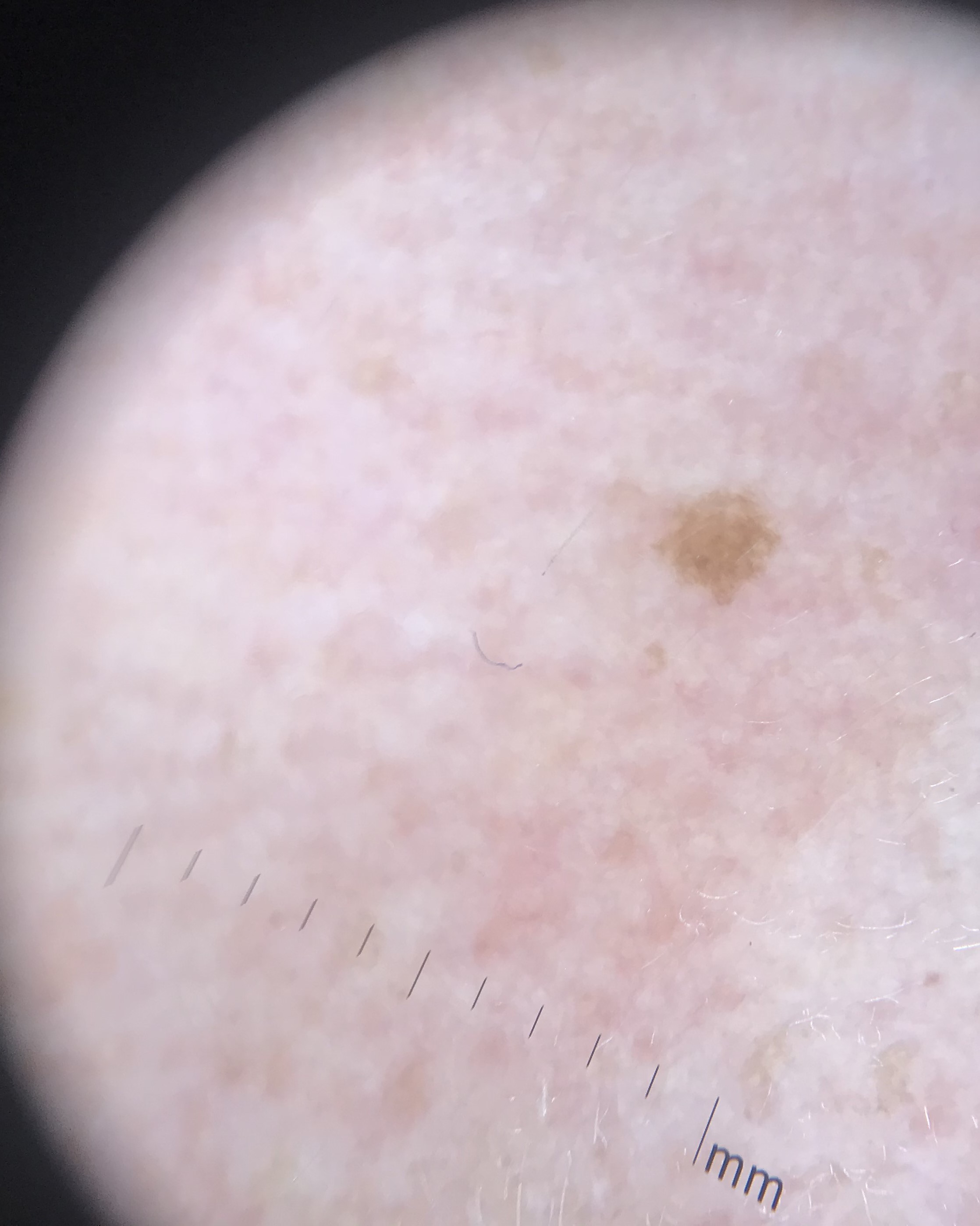Consistent with a seborrheic keratosis.